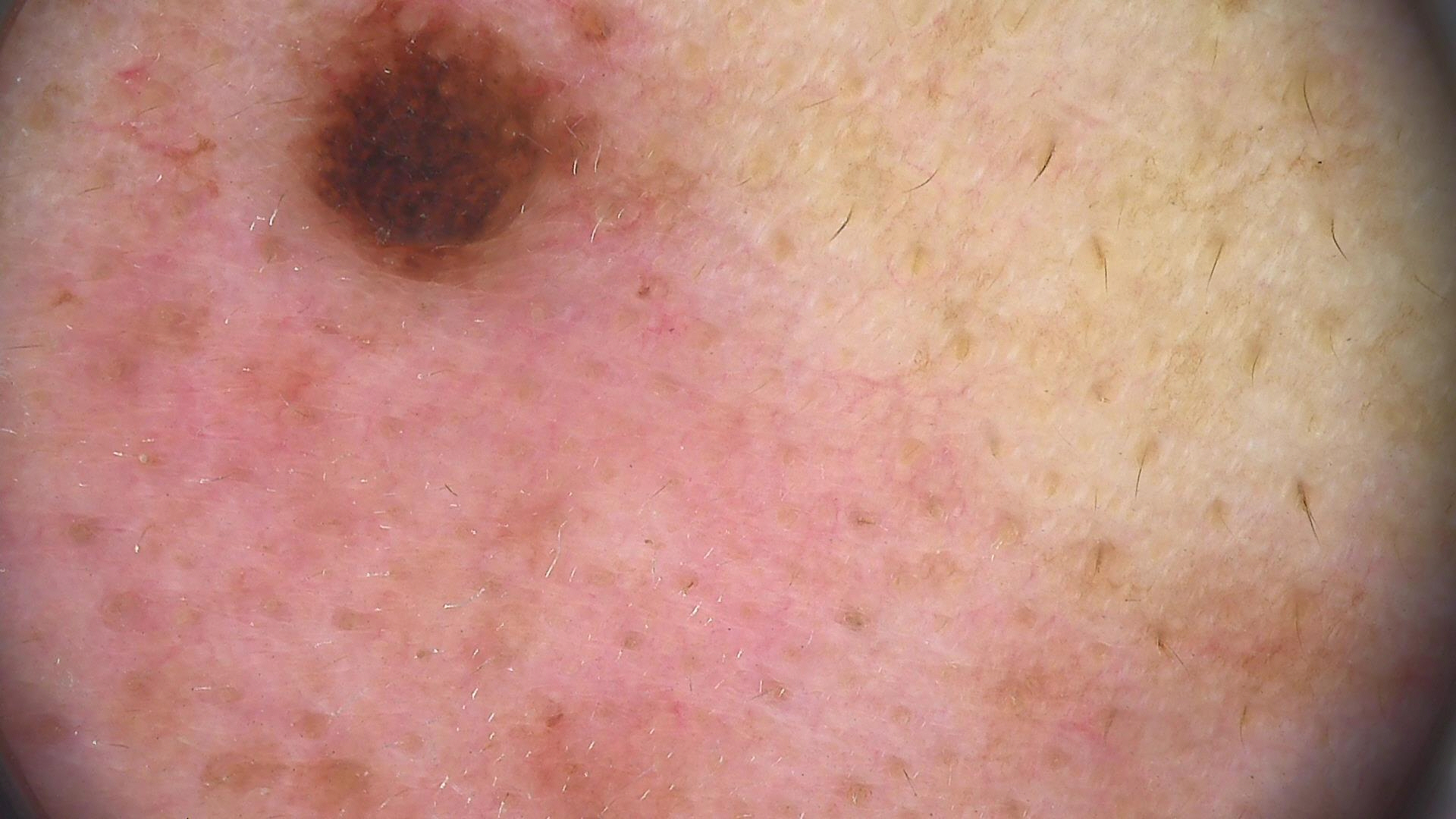Impression:
The diagnosis was a compound nevus.